Close-up view · skin tone: Fitzpatrick II:
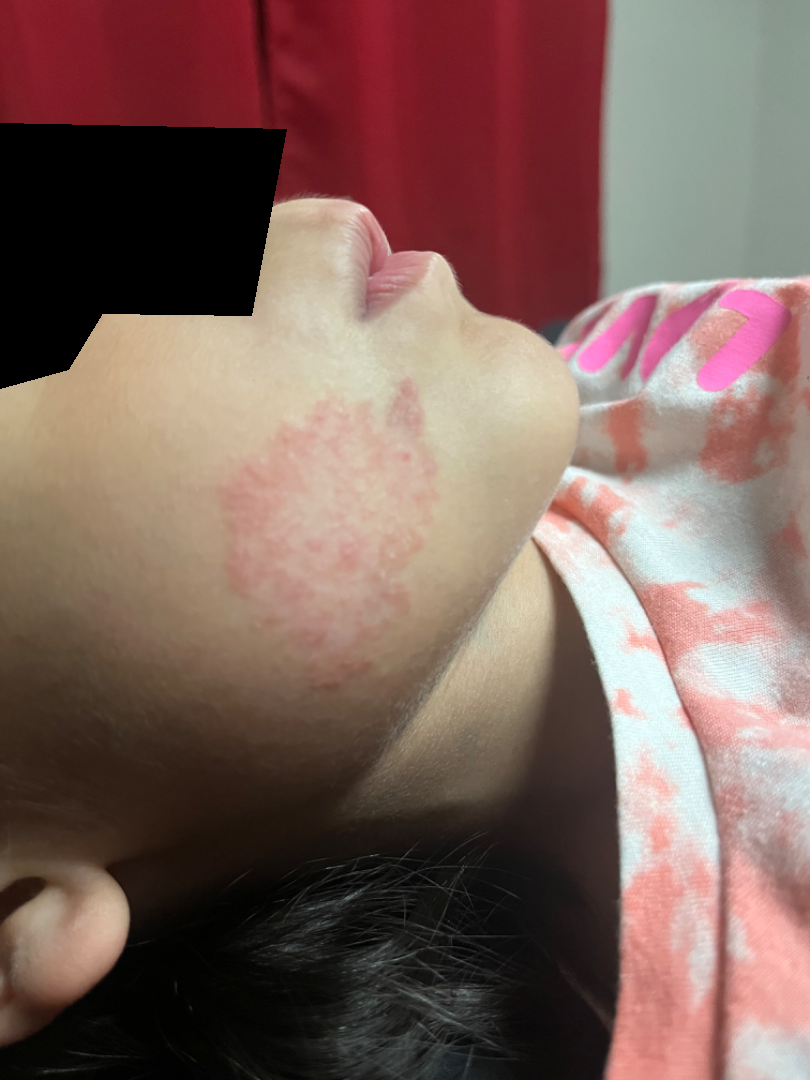impression = Hemangioma (67%); Granuloma faciale (33%)